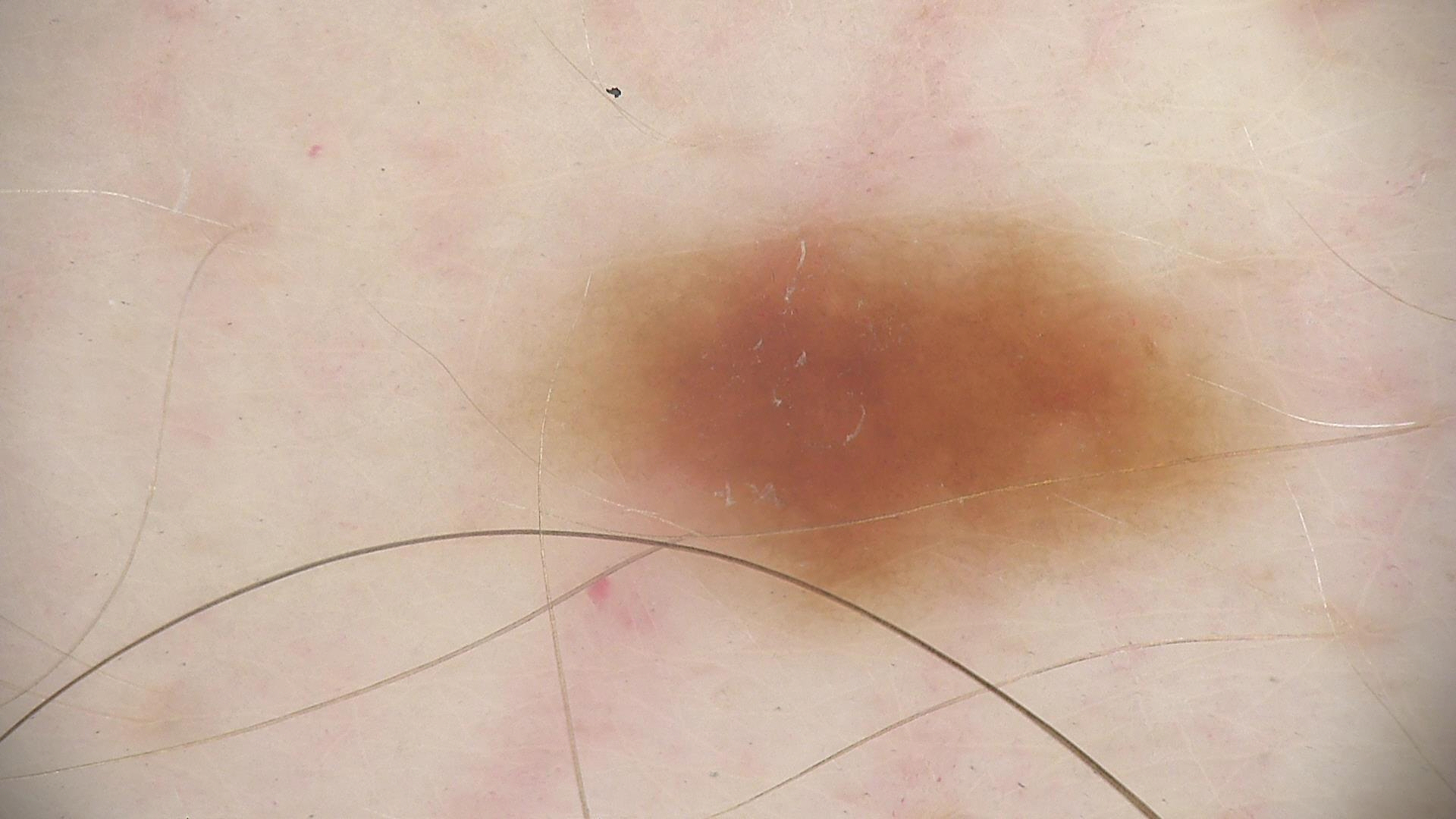imaging: dermatoscopy; diagnosis: dysplastic junctional nevus (expert consensus).